A close-up photograph — 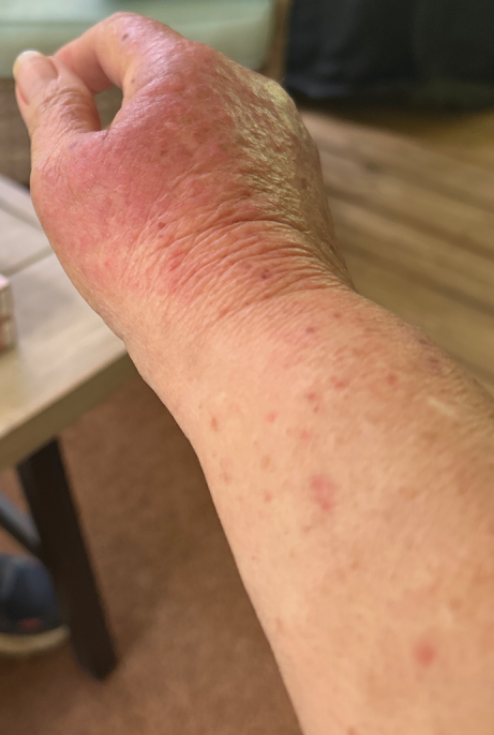assessment: indeterminate from the photograph.